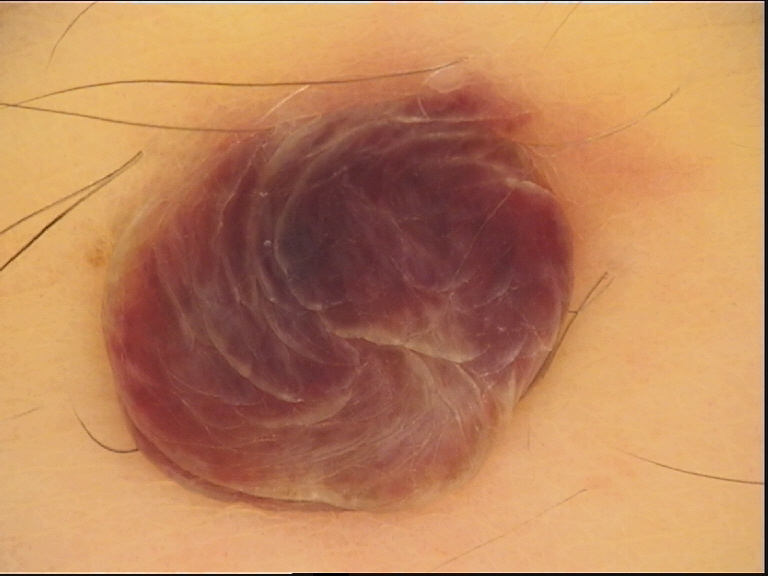<dermoscopy>
<image>dermoscopy</image>
<lesion_type>
<main_class>banal</main_class>
<pattern>dermal</pattern>
</lesion_type>
<diagnosis>
<name>dermal nevus</name>
<code>db</code>
<malignancy>benign</malignancy>
<super_class>melanocytic</super_class>
<confirmation>expert consensus</confirmation>
</diagnosis>
</dermoscopy>